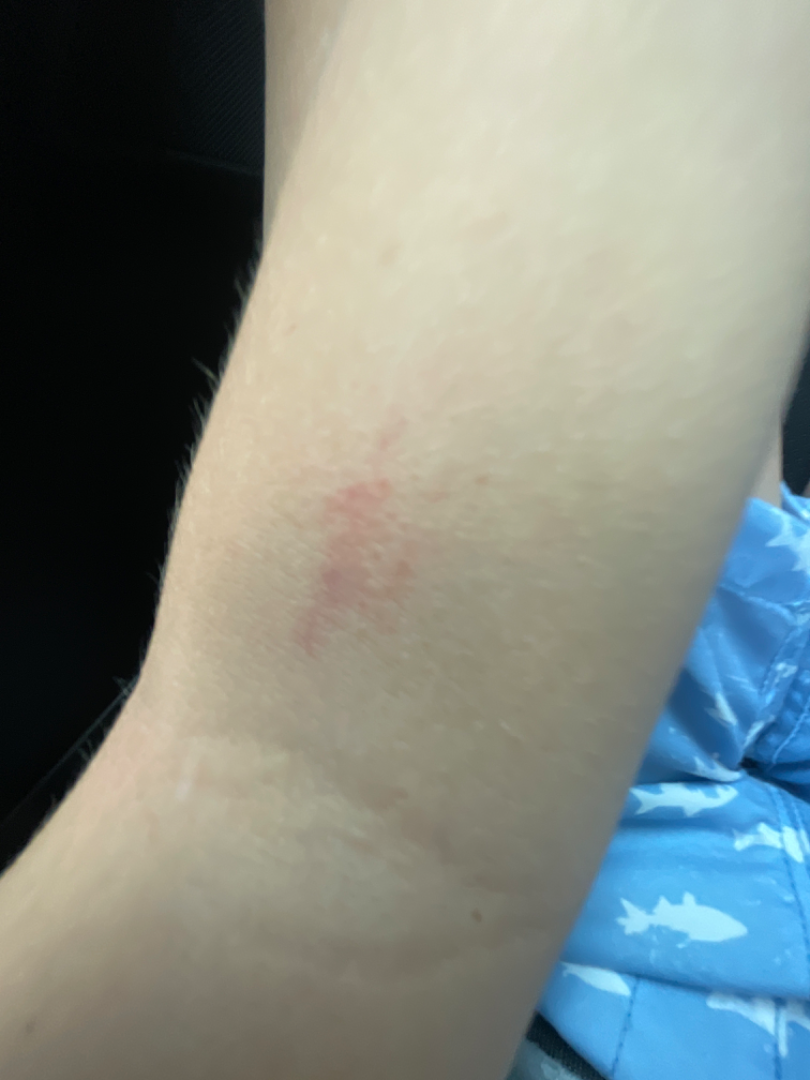  assessment: ungradable on photographic review